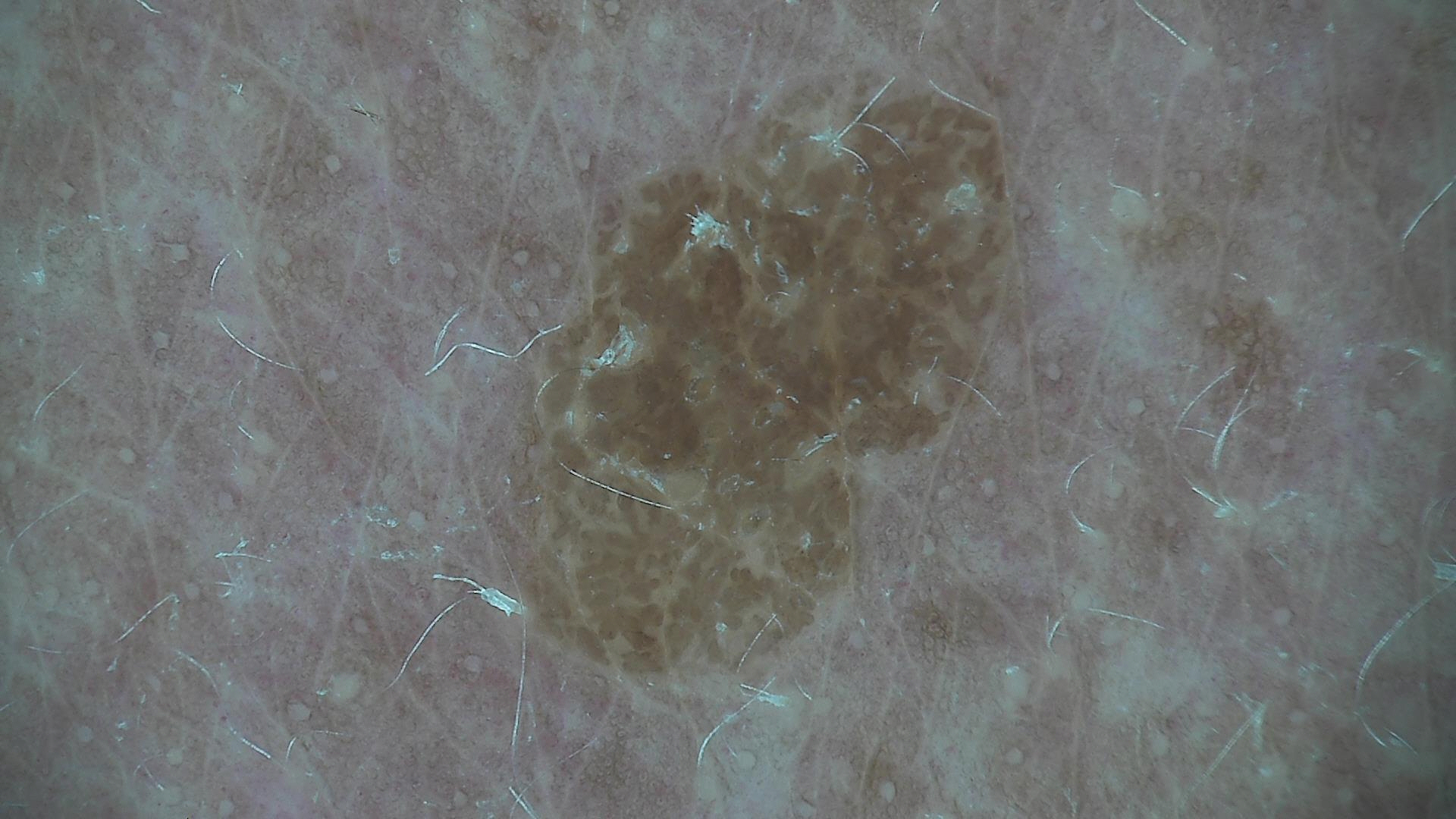Summary: Dermoscopy of a skin lesion. Conclusion: The diagnostic label was a keratinocytic, benign lesion — a seborrheic keratosis.